A smartphone photograph of a skin lesion — 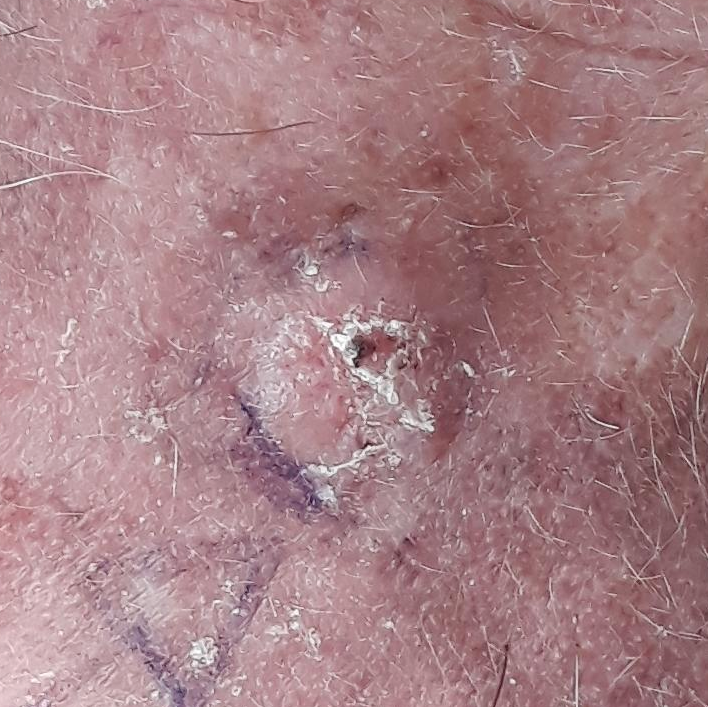* lesion size: 10 × 10 mm
* reported symptoms: bleeding, elevation, pain, growth, itching
* diagnosis: basal cell carcinoma (biopsy-proven)